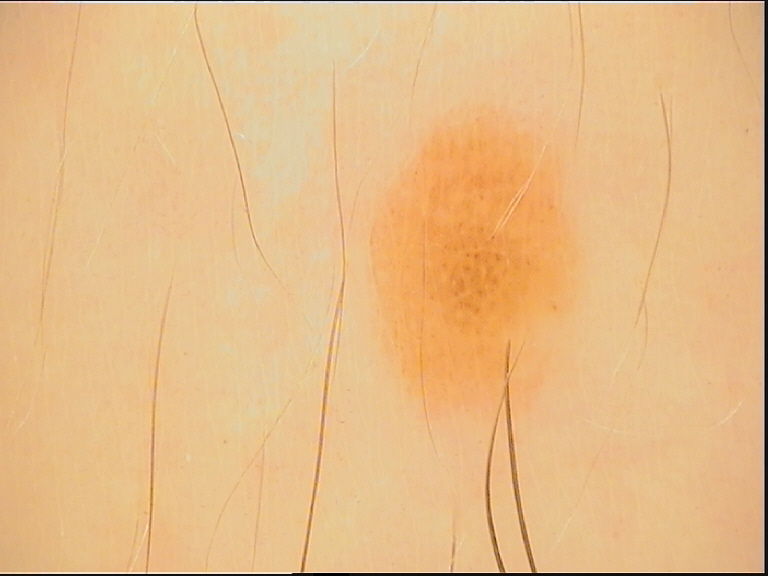Conclusion:
Diagnosed as a dysplastic compound nevus.